Symptoms reported: itching, Fitzpatrick skin type IV, present for less than one week, the patient described the issue as a rash, no constitutional symptoms were reported, the lesion involves the leg, the lesion is described as raised or bumpy, this image was taken at a distance:
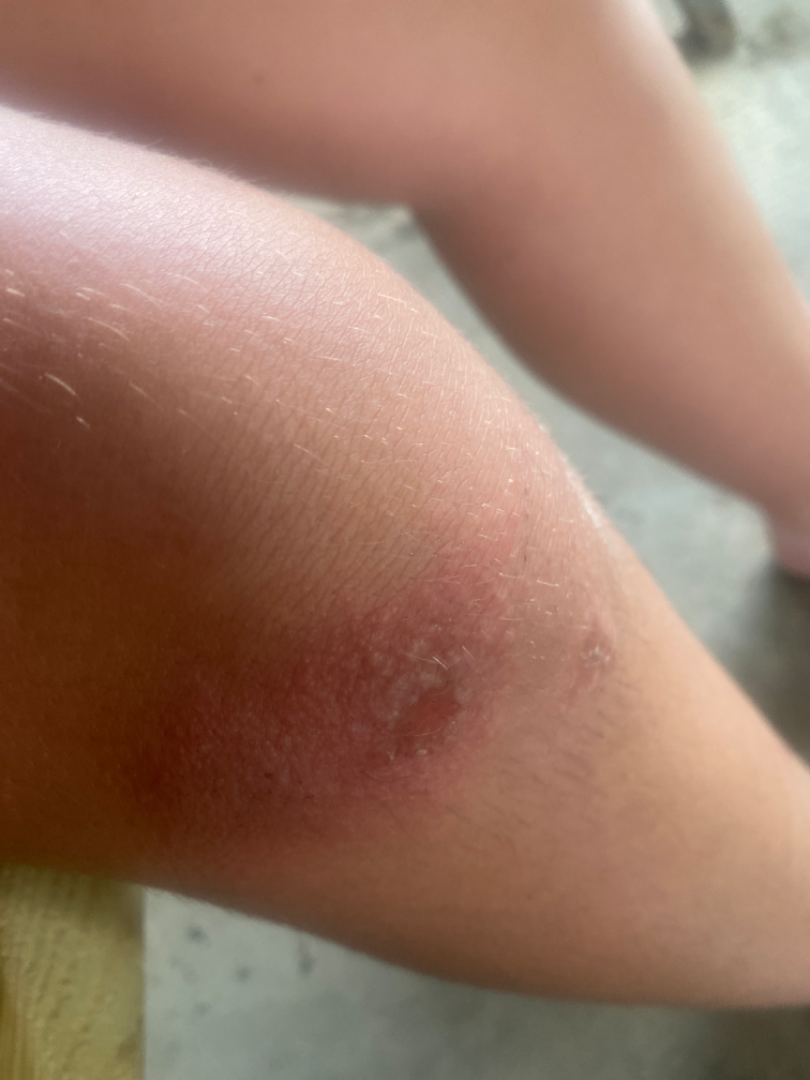Assessment:
The reviewing dermatologist was unable to assign a differential diagnosis from the image.